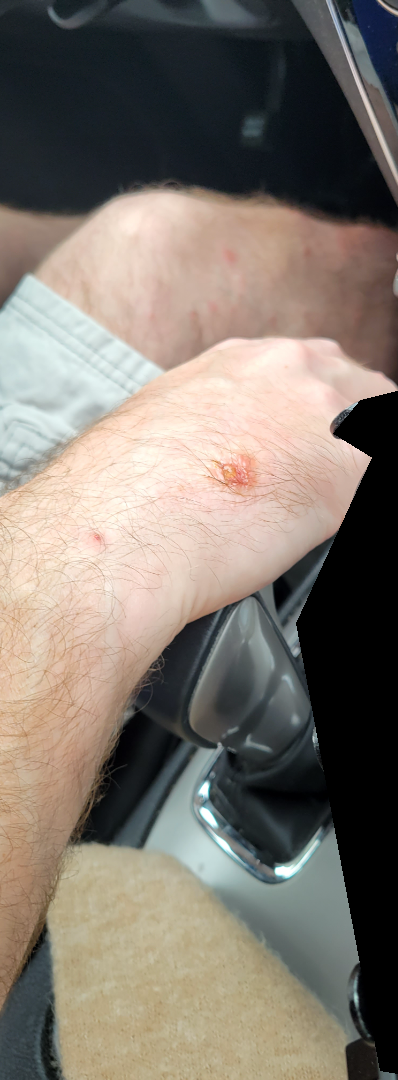• duration · one to four weeks
• patient's own categorization · a rash
• lesion texture · fluid-filled and raised or bumpy
• lesion symptoms · enlargement, bothersome appearance, itching and burning
• constitutional symptoms · none reported
• image framing · at an angle
• body site · leg, arm and back of the torso
• impression · consistent with Allergic Contact Dermatitis